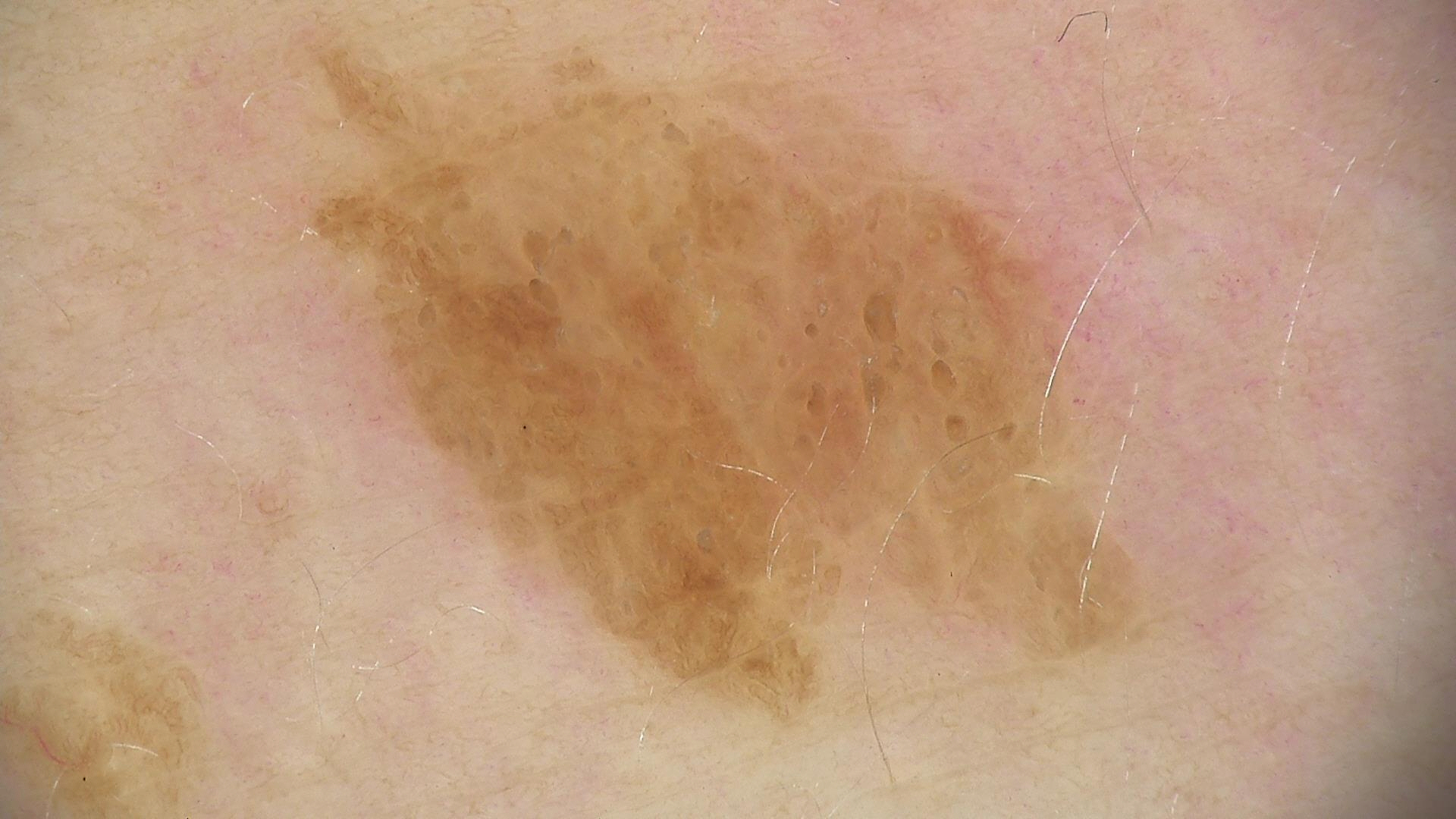Labeled as a keratinocytic lesion — a seborrheic keratosis.